A female subject aged 42 · the patient is Fitzpatrick I · a smartphone photograph of a skin lesion.
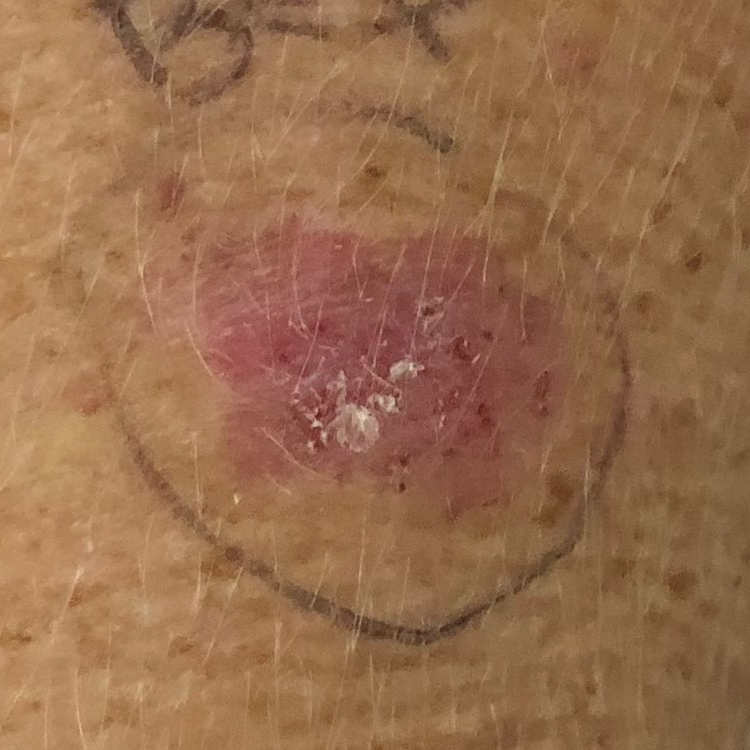| key | value |
|---|---|
| body site | an arm |
| diameter | approx. 20 × 12 mm |
| symptoms | elevation, itching / no growth |
| diagnostic label | basal cell carcinoma (biopsy-proven) |